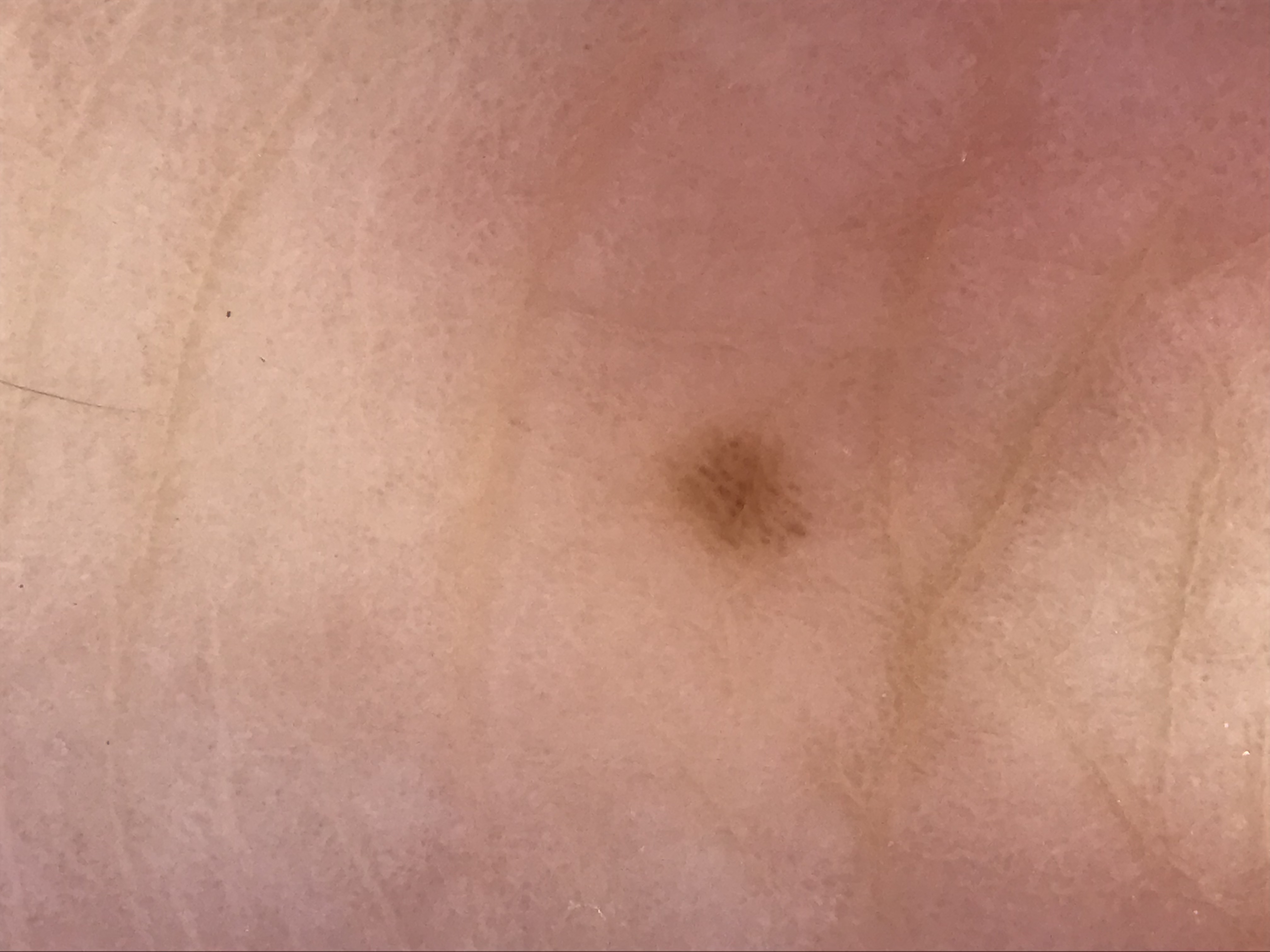A dermoscopic image of a skin lesion. This is a banal lesion. The diagnosis was an acral junctional nevus.